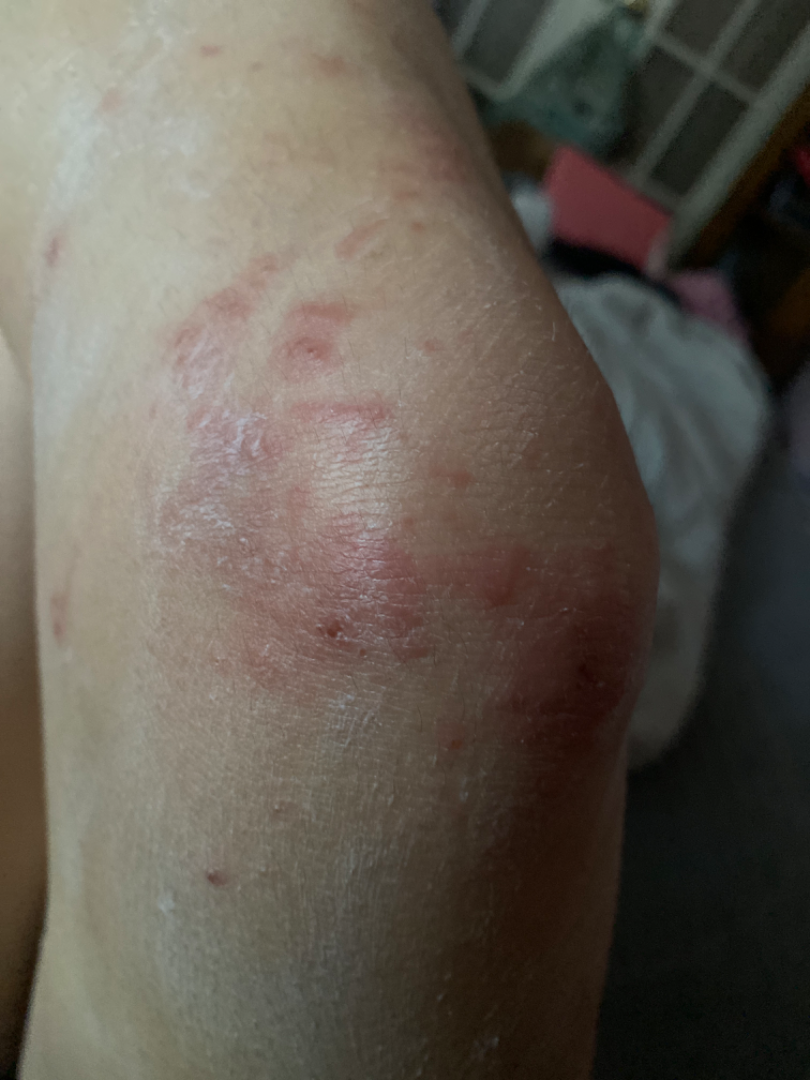The skin findings could not be characterized from the image. The photograph is a close-up of the affected area. The lesion involves the leg. The patient indicates the condition has been present for less than one week.